A dermoscopic photograph of a skin lesion.
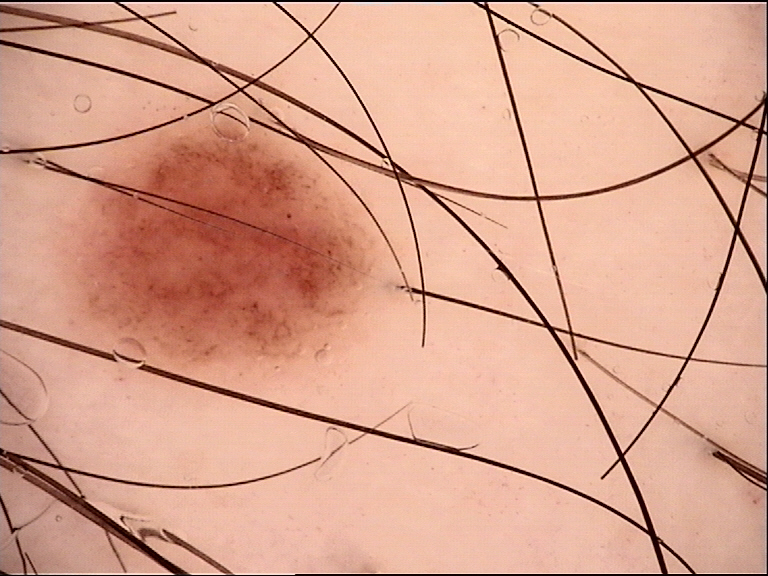diagnosis:
  name: dysplastic junctional nevus
  code: jd
  malignancy: benign
  super_class: melanocytic
  confirmation: expert consensus